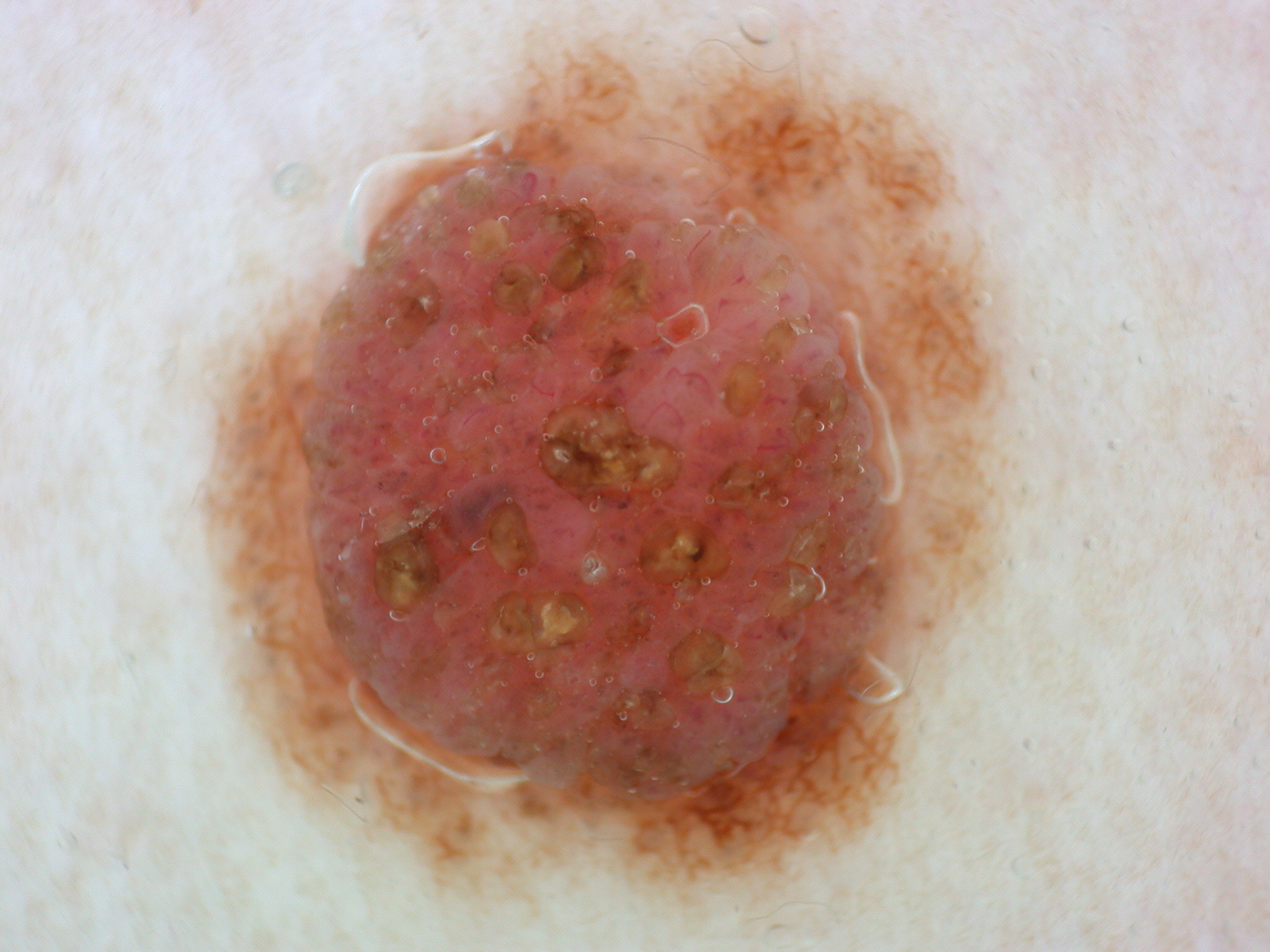Image and clinical context: A dermatoscopic image of a skin lesion. Dermoscopic review identifies pigment network. The lesion covers approximately 42% of the dermoscopic field. Lesion location: x1=210 y1=45 x2=1004 y2=905. Conclusion: Expert review diagnosed this as a melanocytic nevus, a benign skin lesion.